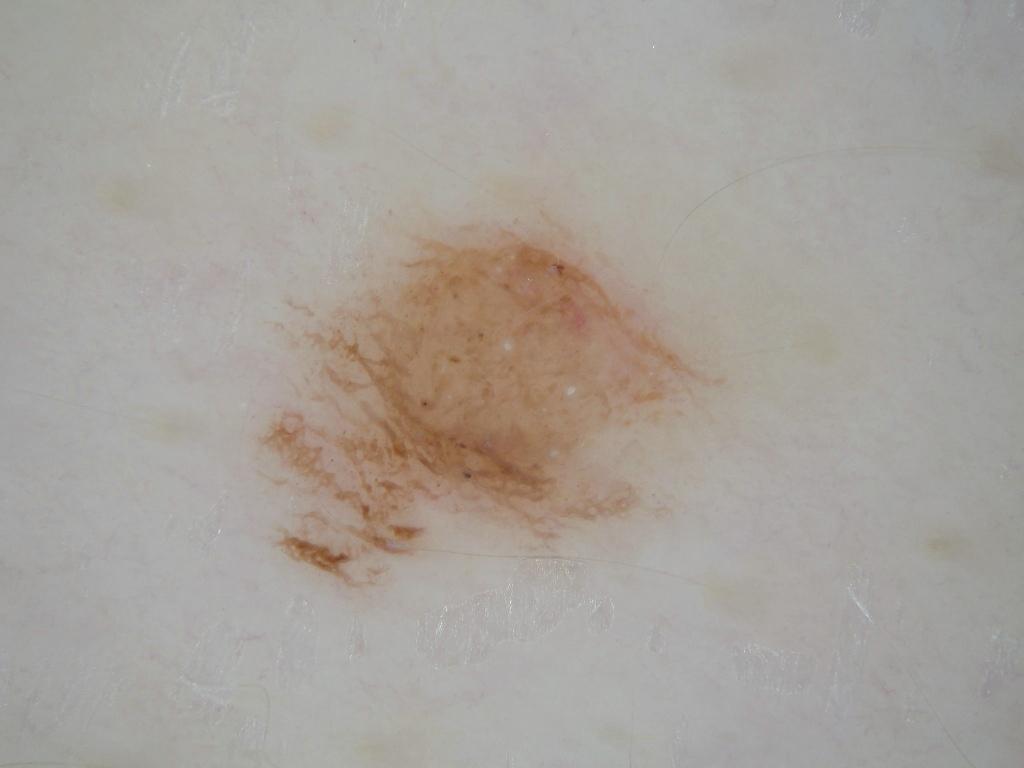– image — dermoscopy
– bounding box — 254 180 732 590
– impression — a melanocytic nevus, a benign skin lesion